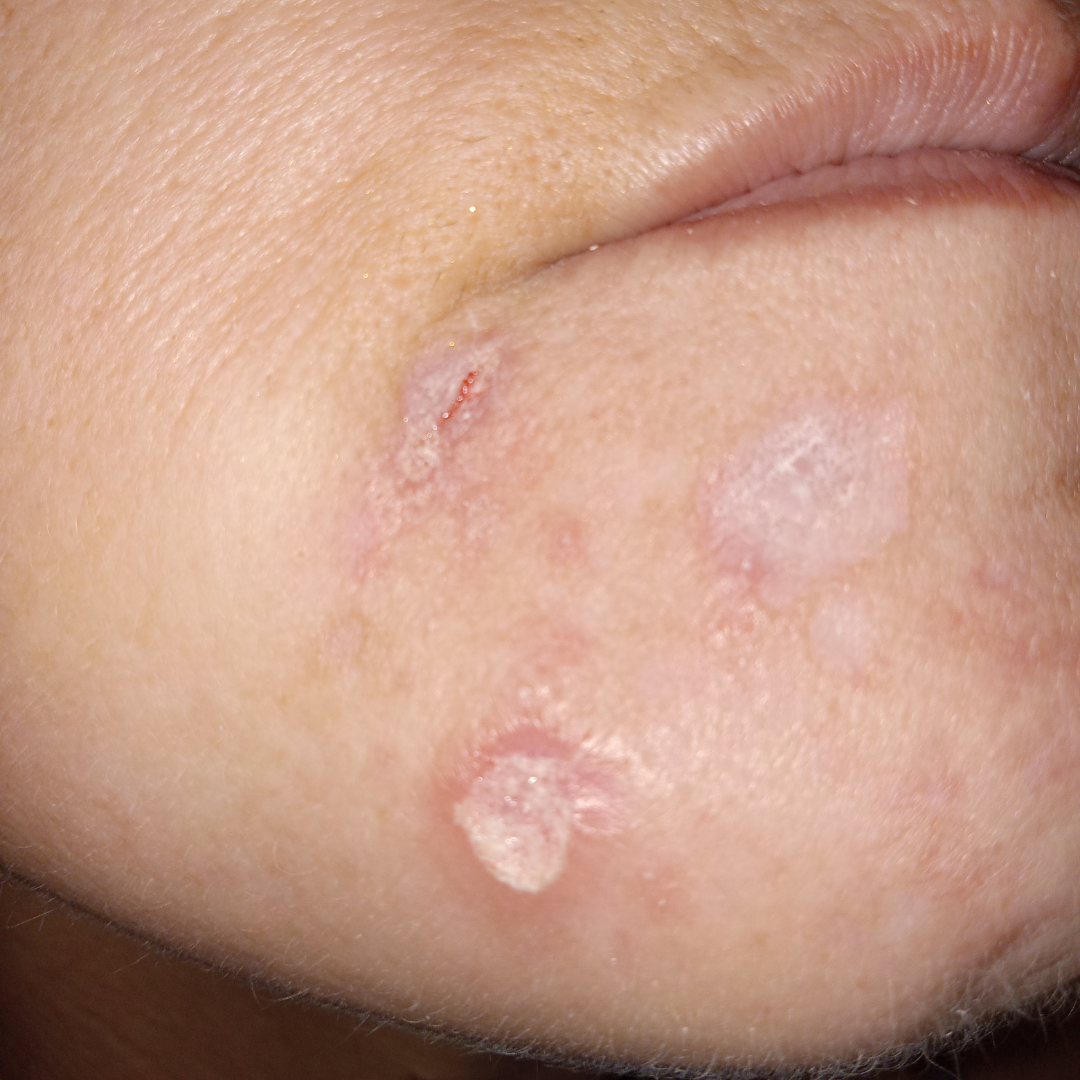<report>
  <assessment>ungradable on photographic review</assessment>
  <patient>female, age 40–49</patient>
  <duration>three to twelve months</duration>
  <shot_type>at an angle</shot_type>
  <patient_category>a rash</patient_category>
  <systemic_symptoms>mouth sores, shortness of breath</systemic_symptoms>
  <texture>raised or bumpy, rough or flaky</texture>
  <symptoms>bleeding, itching, bothersome appearance, burning</symptoms>
  <body_site>head or neck</body_site>
</report>